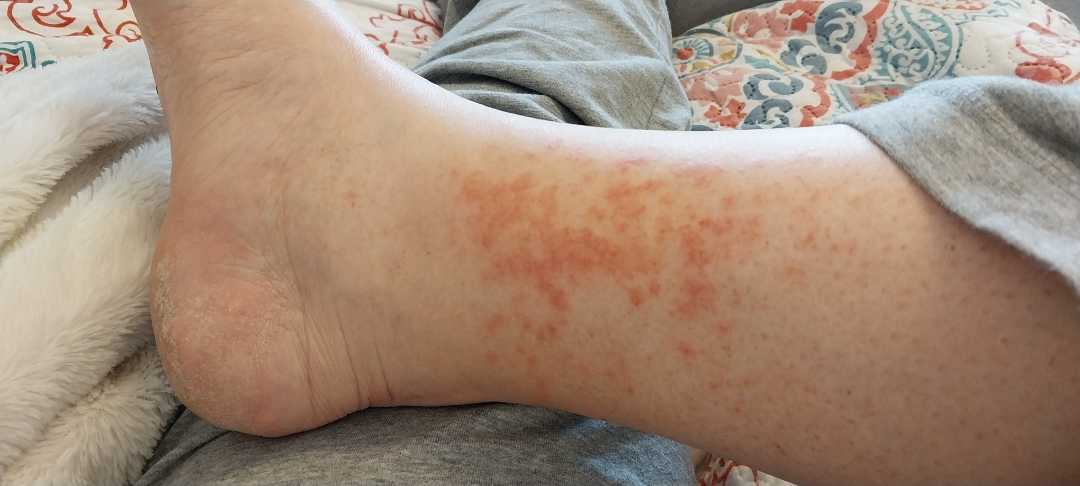No differential diagnosis could be assigned on photographic review.
Skin tone: Fitzpatrick phototype II; non-clinician graders estimated a Monk skin tone scale of 2.
This image was taken at a distance.